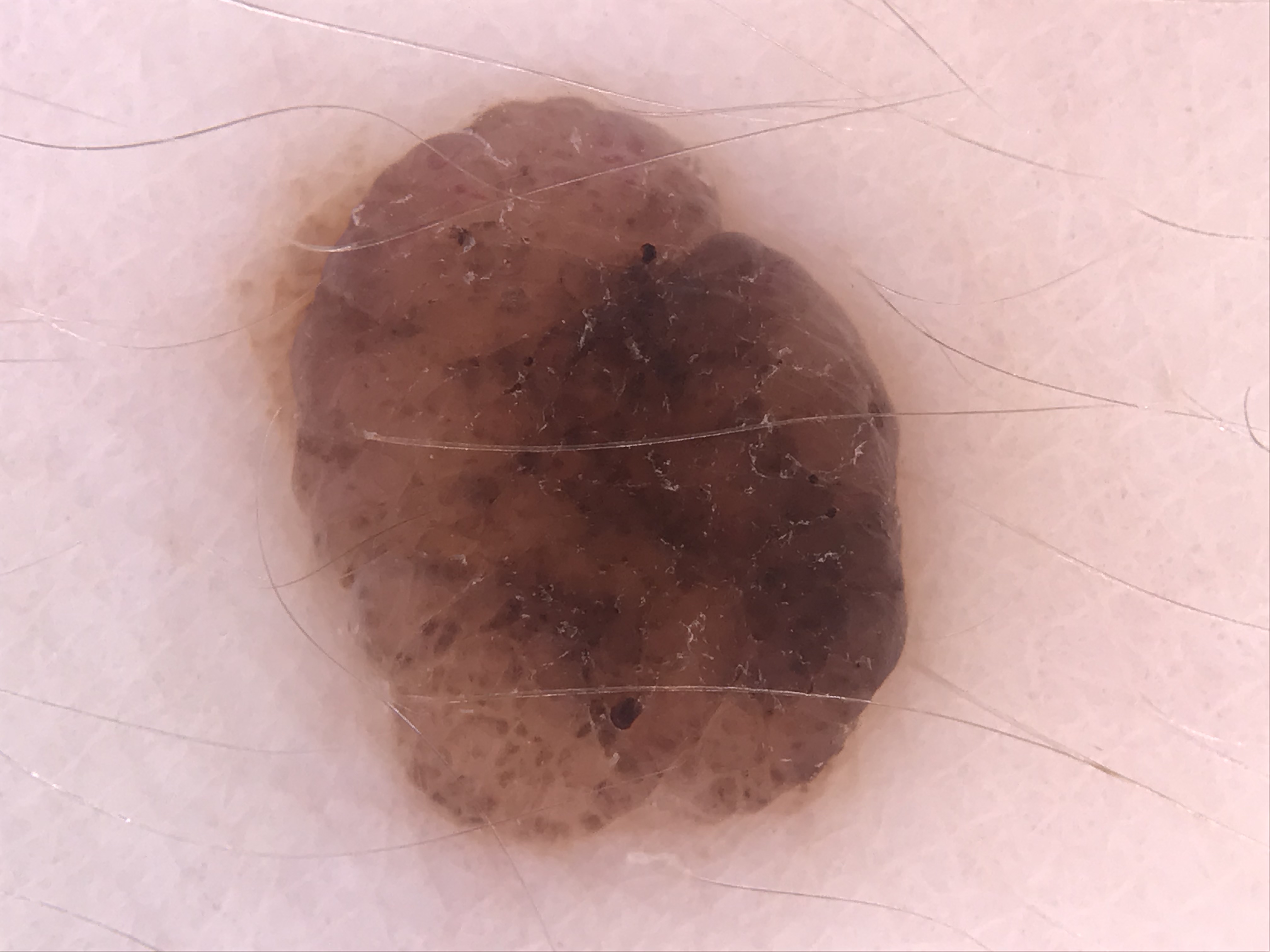A dermatoscopic image of a skin lesion. Labeled as a banal lesion — a compound nevus.